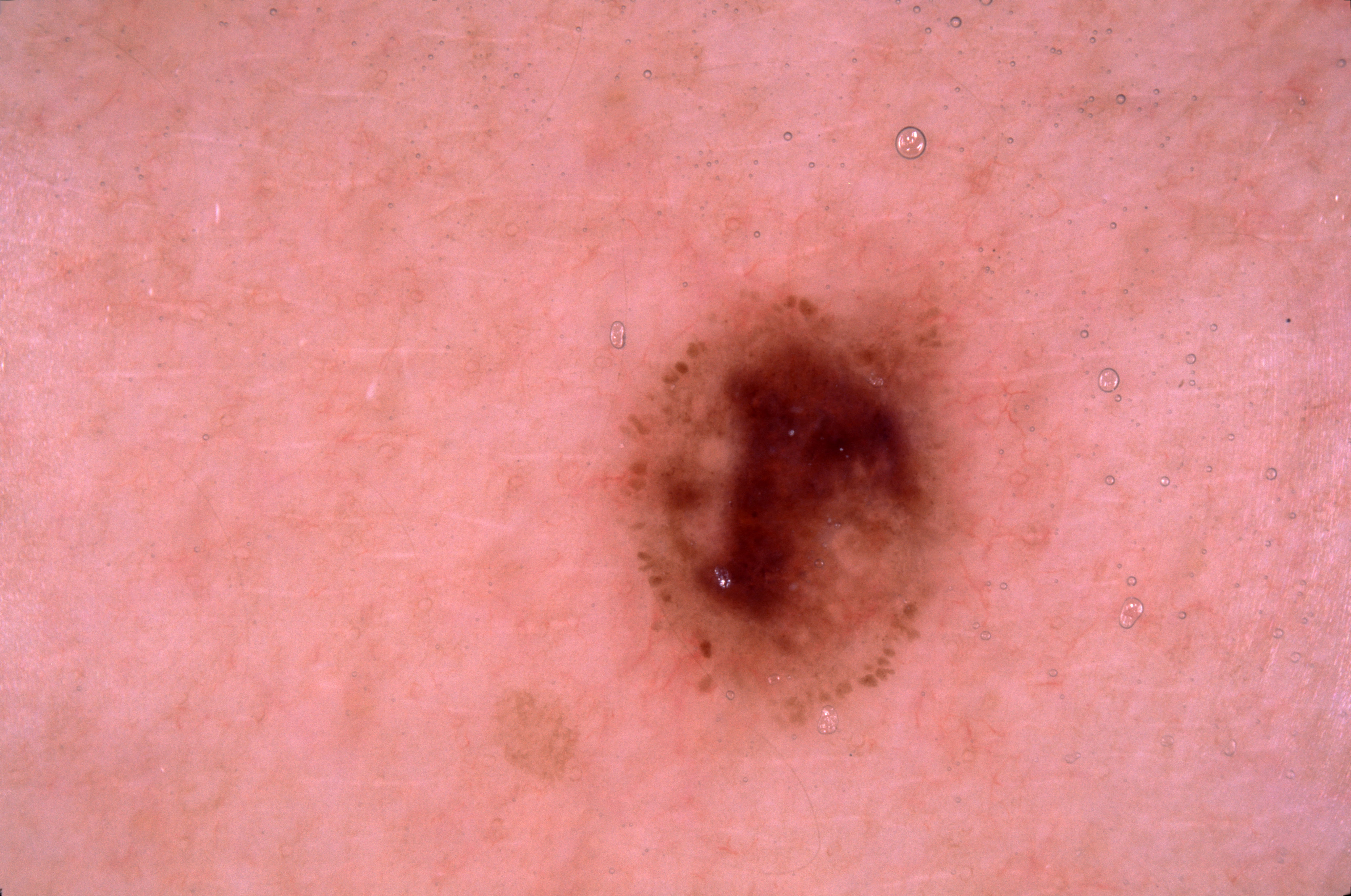A dermatoscopic image of a skin lesion.
As (left, top, right, bottom), the lesion spans box(612, 280, 975, 727).
Dermoscopic assessment notes no pigment network, milia-like cysts, negative network, or streaks.
The lesion covers approximately 9% of the dermoscopic field.
On biopsy, the diagnosis was a melanoma, a malignant lesion.